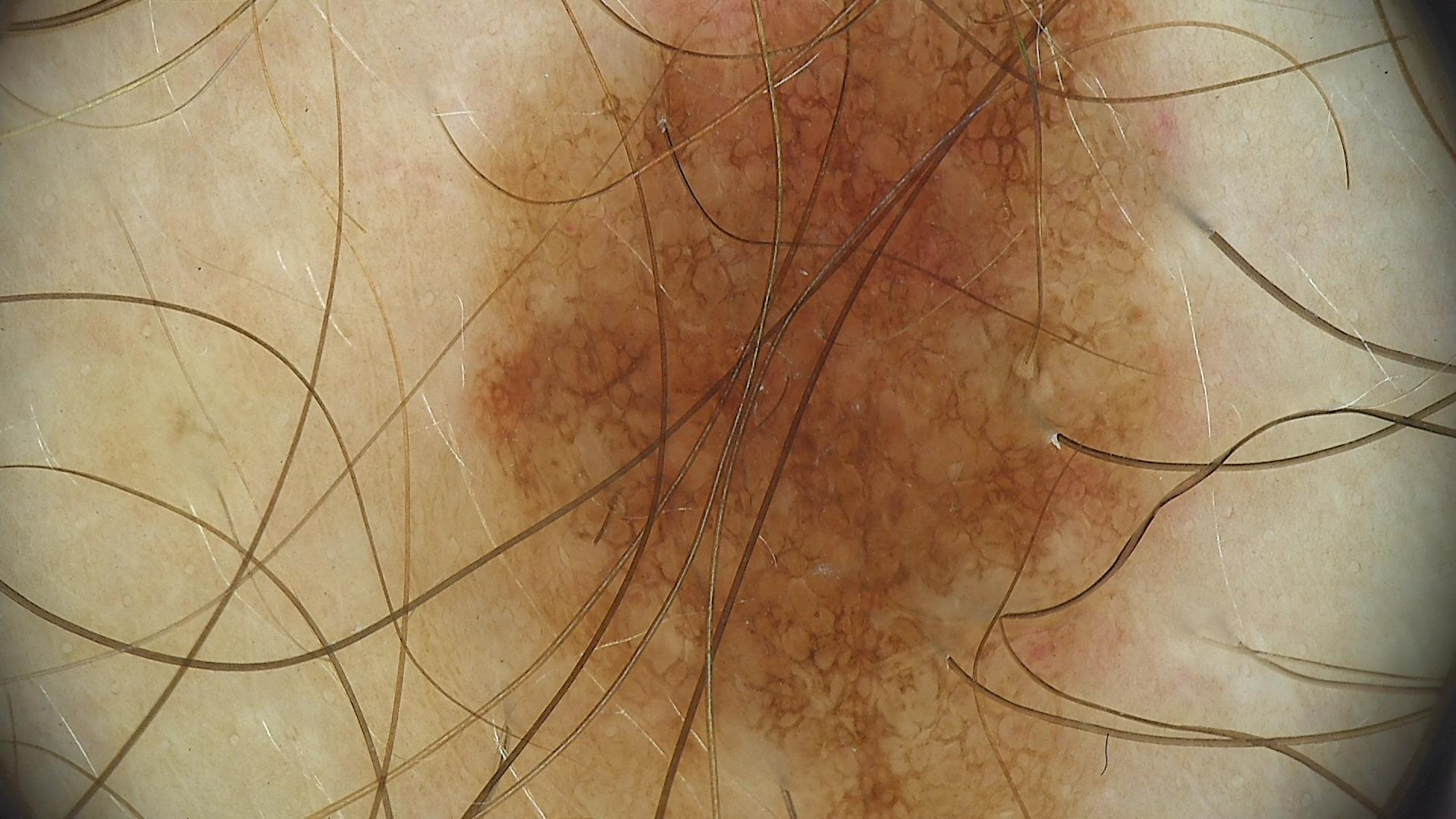assessment: dysplastic junctional nevus (expert consensus)